A dermoscopic close-up of a skin lesion: 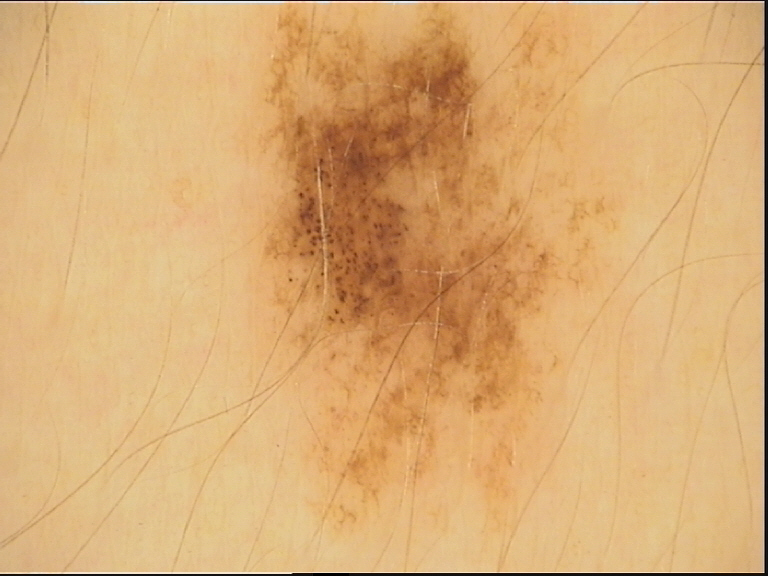Impression: The diagnosis was a dysplastic junctional nevus.